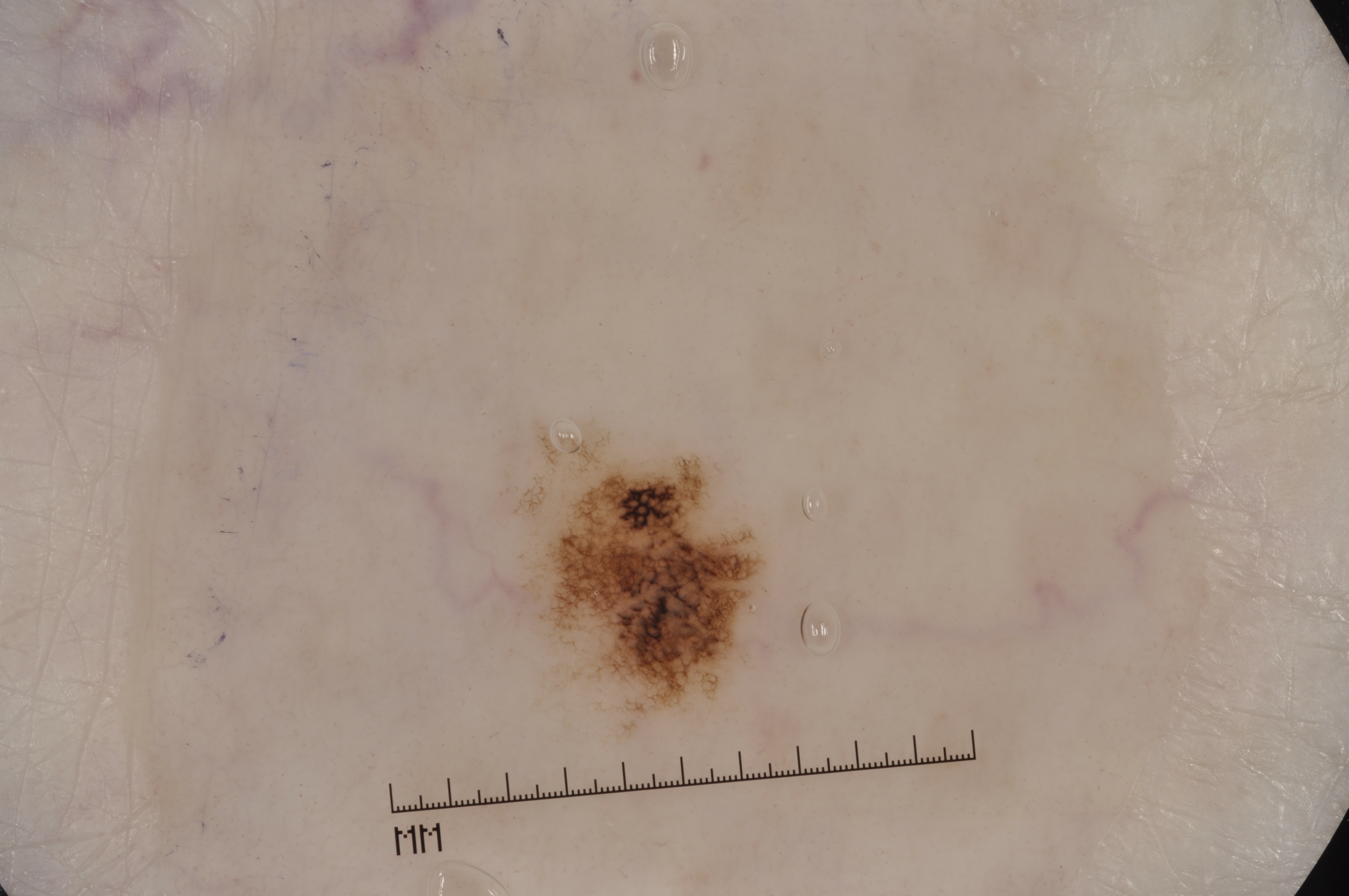subject: female, in their 60s; image type: dermoscopy of a skin lesion; lesion extent: small; bounding box: box(527, 441, 759, 707); features: pigment network; diagnosis: a melanocytic nevus, a benign lesion.